Dermoscopy of a skin lesion.
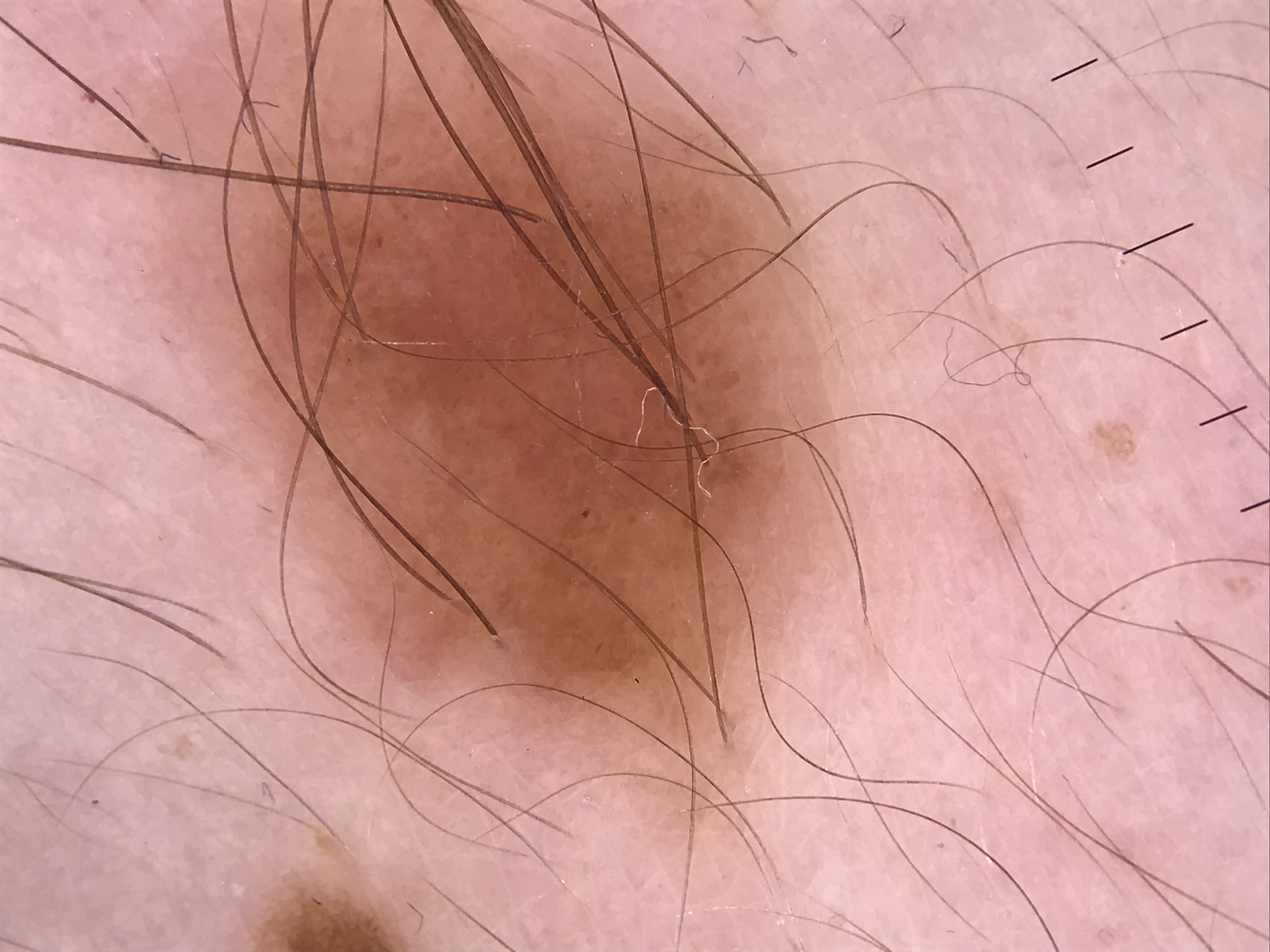Case: The architecture is that of a banal lesion. Conclusion: Diagnosed as a compound nevus.